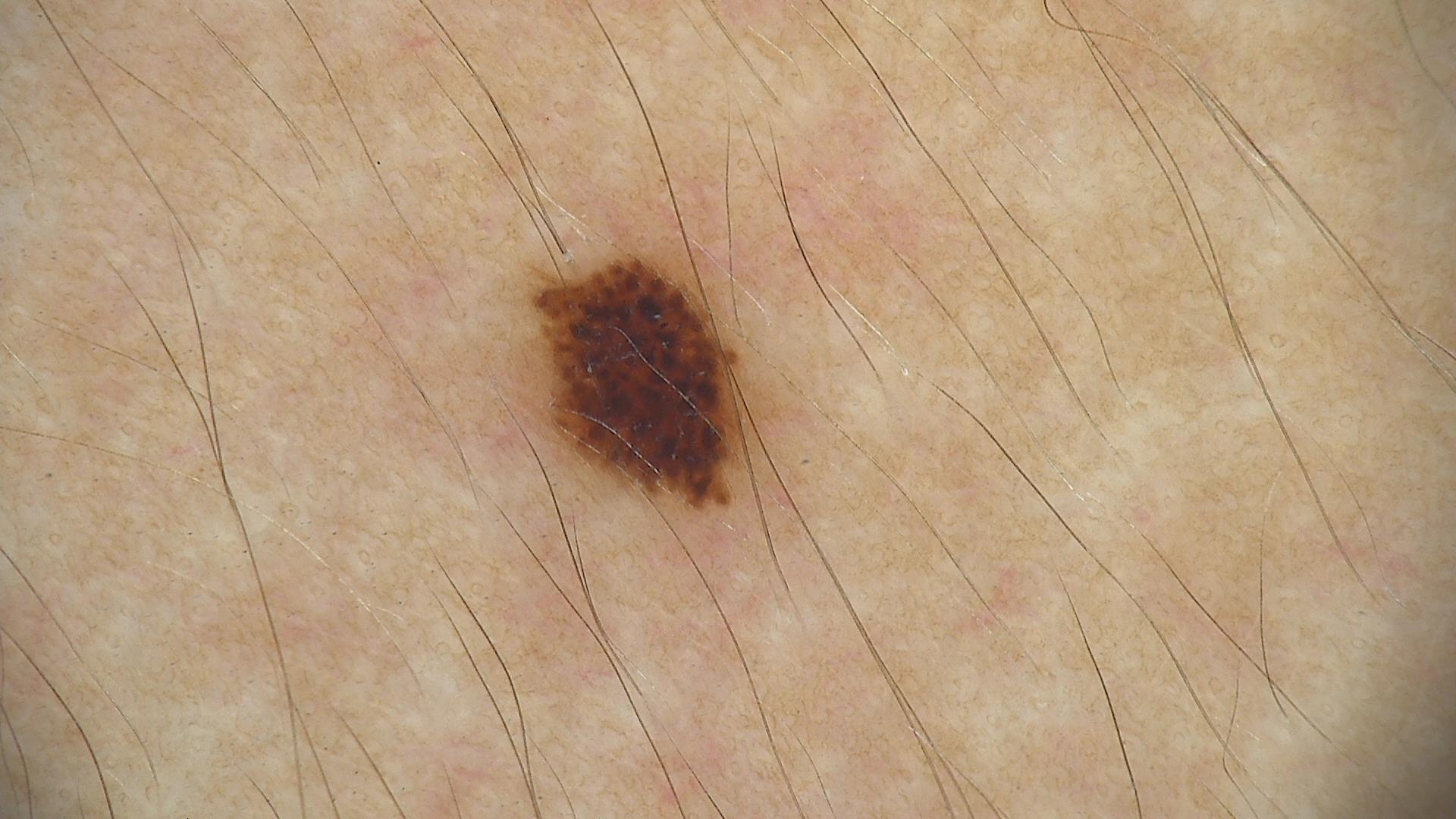A skin lesion imaged with a dermatoscope.
Diagnosed as a benign lesion — a dysplastic junctional nevus.